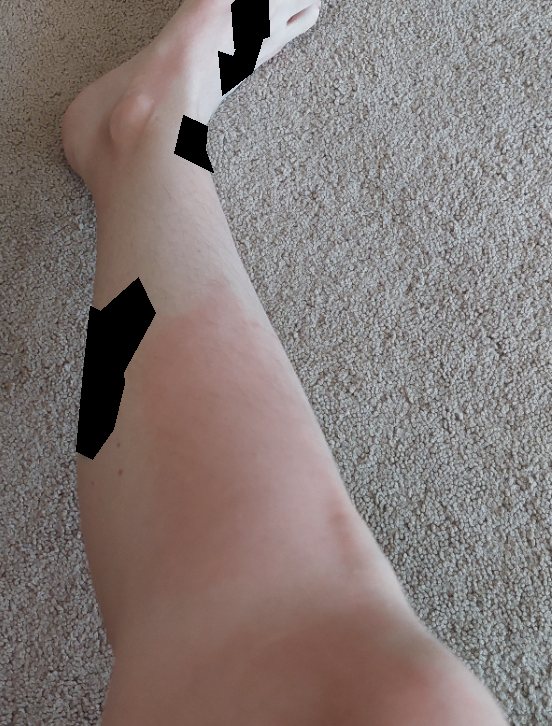Findings:
• symptoms · pain
• body site · top or side of the foot and leg
• skin tone · Fitzpatrick I
• contributor · female, age 30–39
• framing · at a distance
• associated systemic symptoms · none reported
• present for · less than one week
• patient's own categorization · a rash
• differential diagnosis · the leading consideration is Abrasion, scrape, or scab